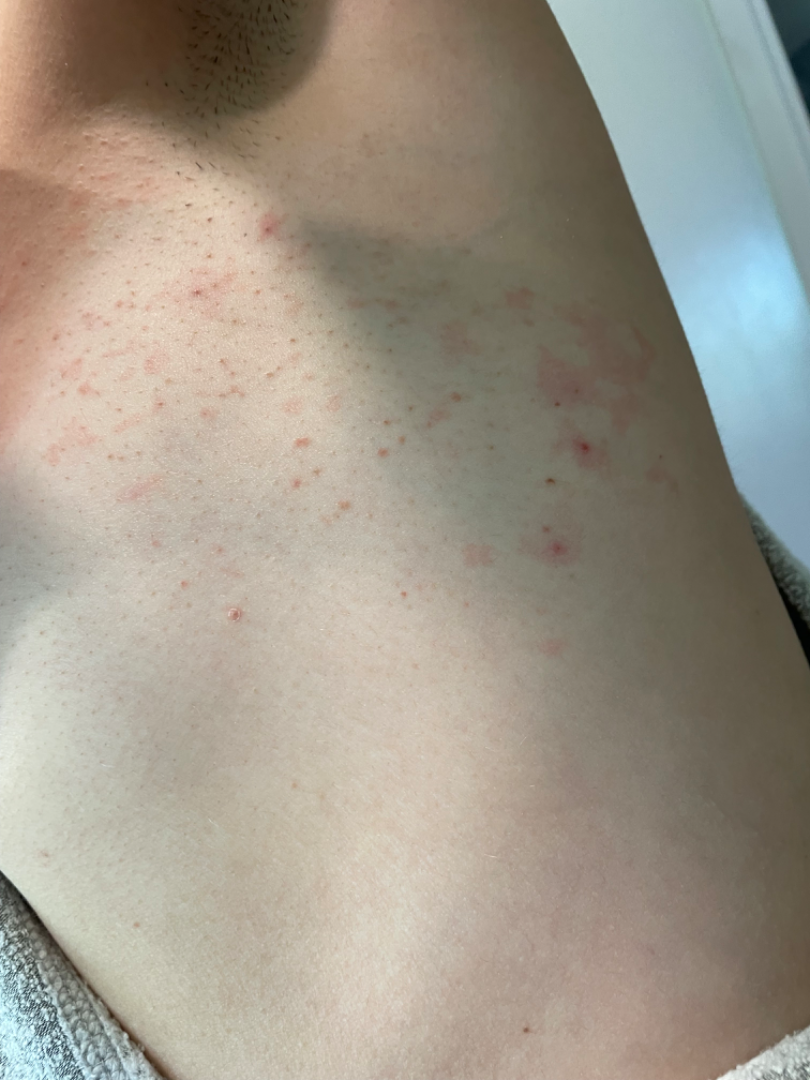The skin findings could not be characterized from the image.